This image was taken at an angle. Located on the leg and arm.
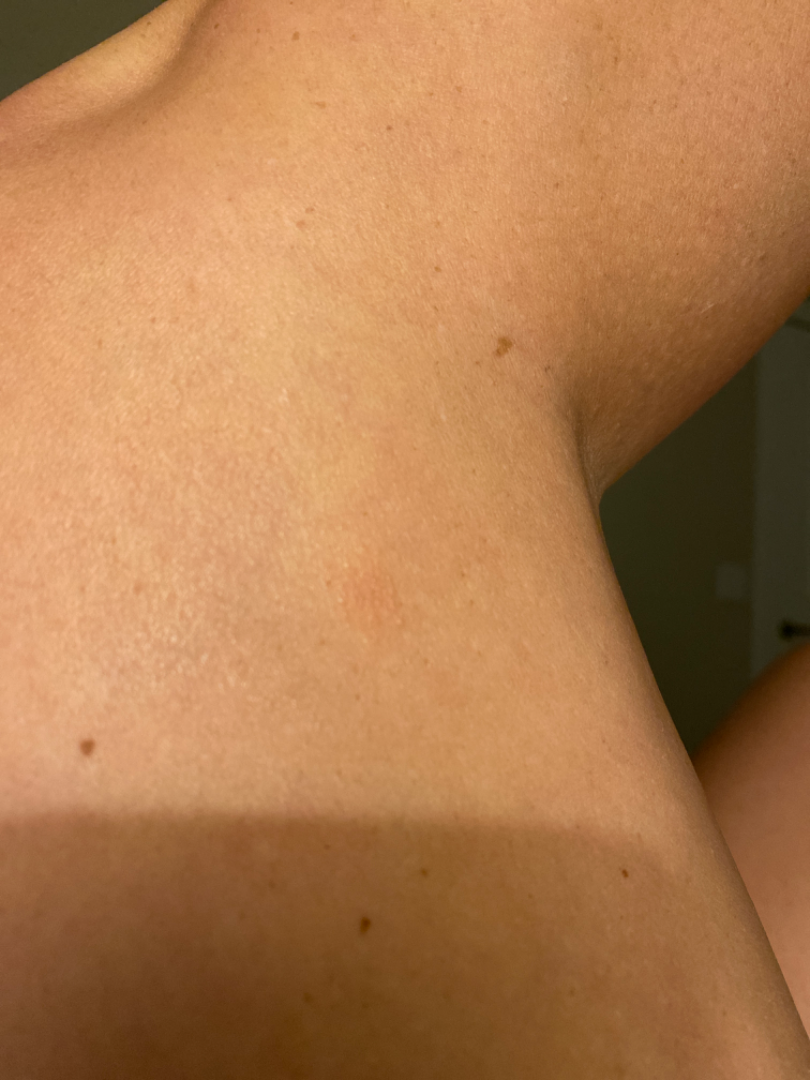Review:
The case was difficult to assess from the available photograph.
Patient information:
Skin tone: FST IV. The condition has been present for less than one week. Texture is reported as raised or bumpy and rough or flaky.